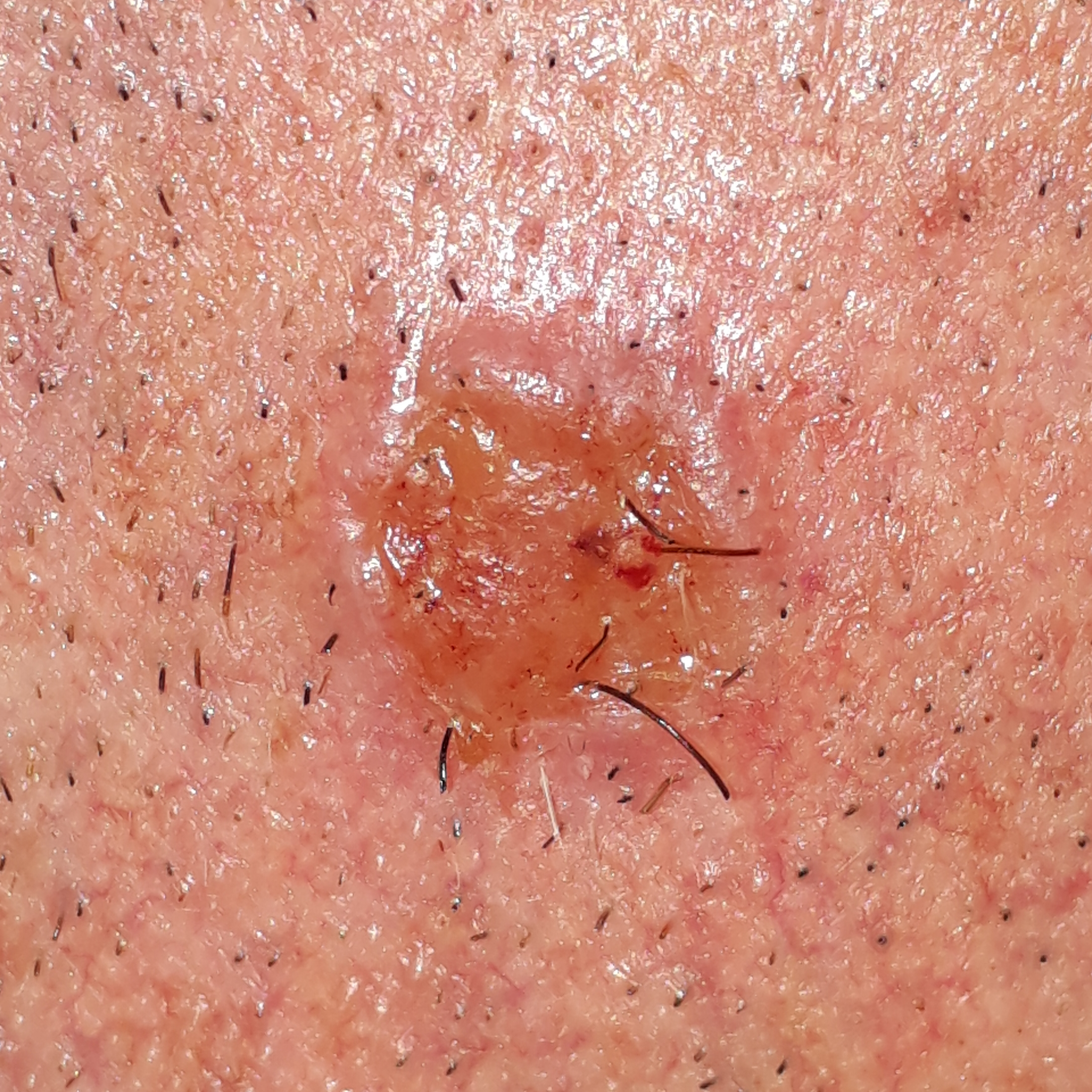Pathology: On biopsy, the diagnosis was a basal cell carcinoma.